The subject is female · the leg, arm and back of the hand are involved · the photograph was taken at an angle — 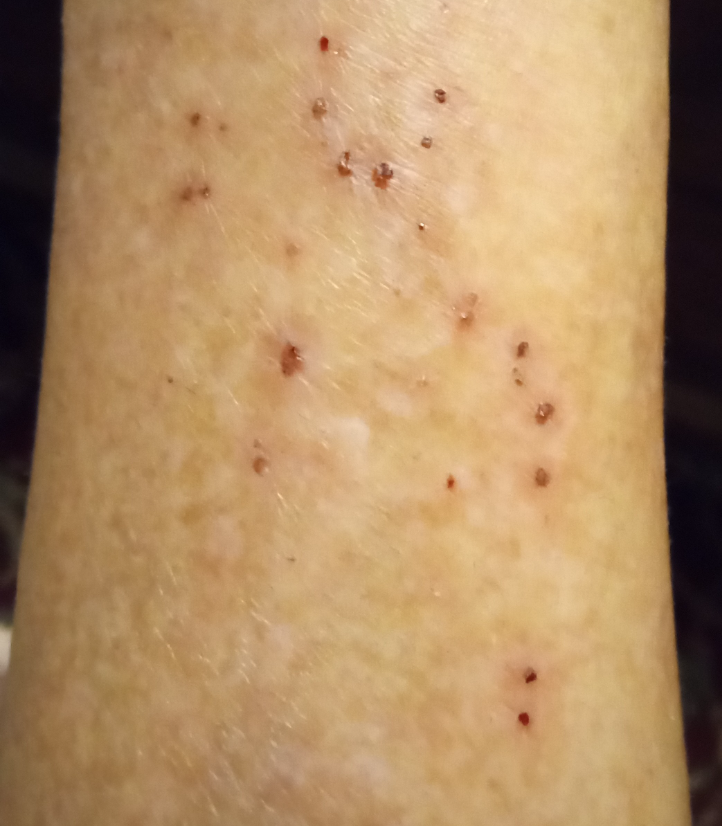Q: What is the lesion texture?
A: raised or bumpy
Q: What symptoms does the patient report?
A: itching
Q: How does the patient describe it?
A: a rash
Q: Constitutional symptoms?
A: none reported
Q: When did this start?
A: more than one year
Q: What is the dermatologist's impression?
A: in keeping with Eczema